A dermoscopic close-up of a skin lesion.
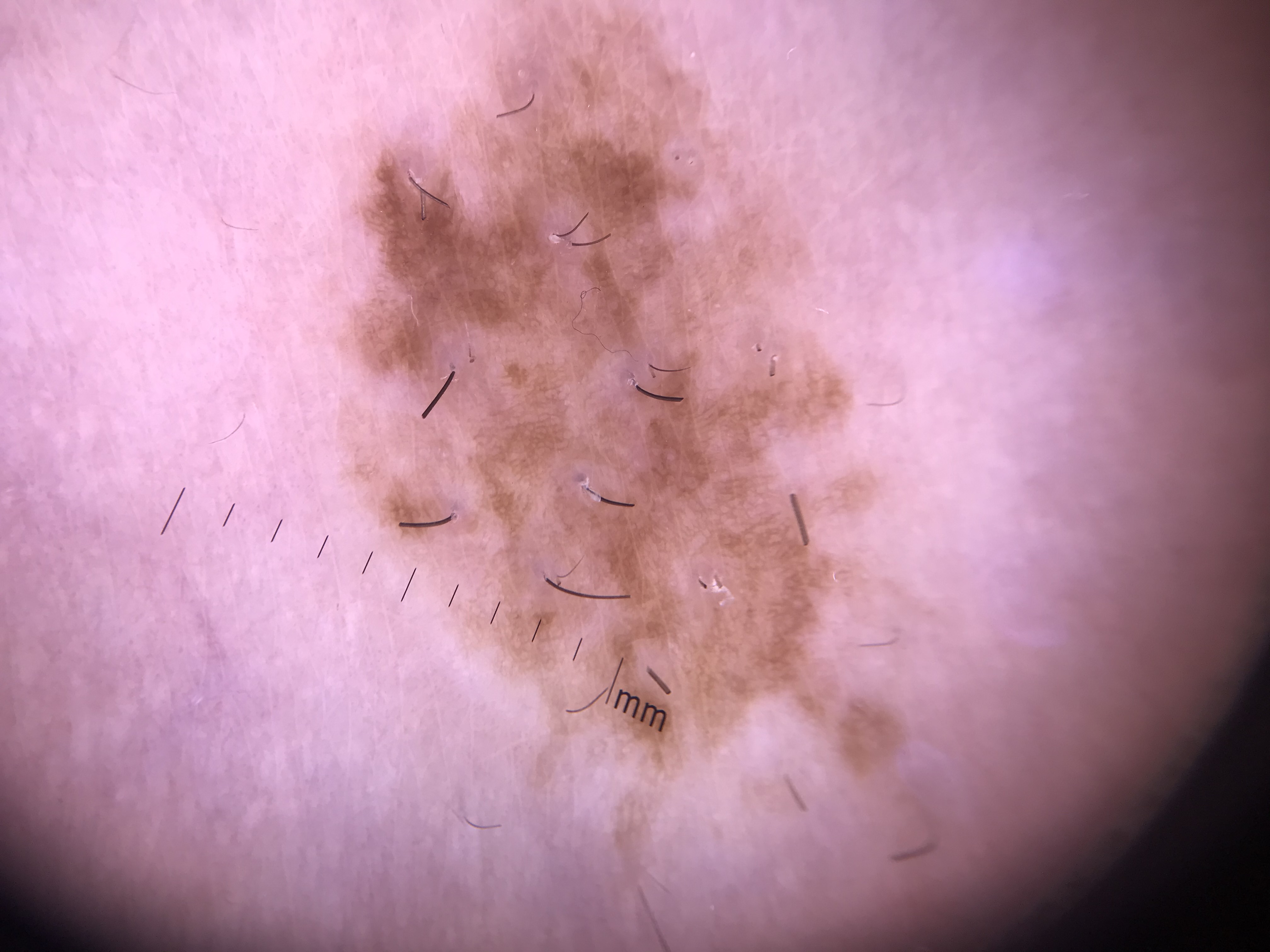Case: This is a banal lesion. Impression: The diagnostic label was a congenital compound nevus.